A smartphone photograph of a skin lesion. The patient is Fitzpatrick phototype III. A male patient in their 30s.
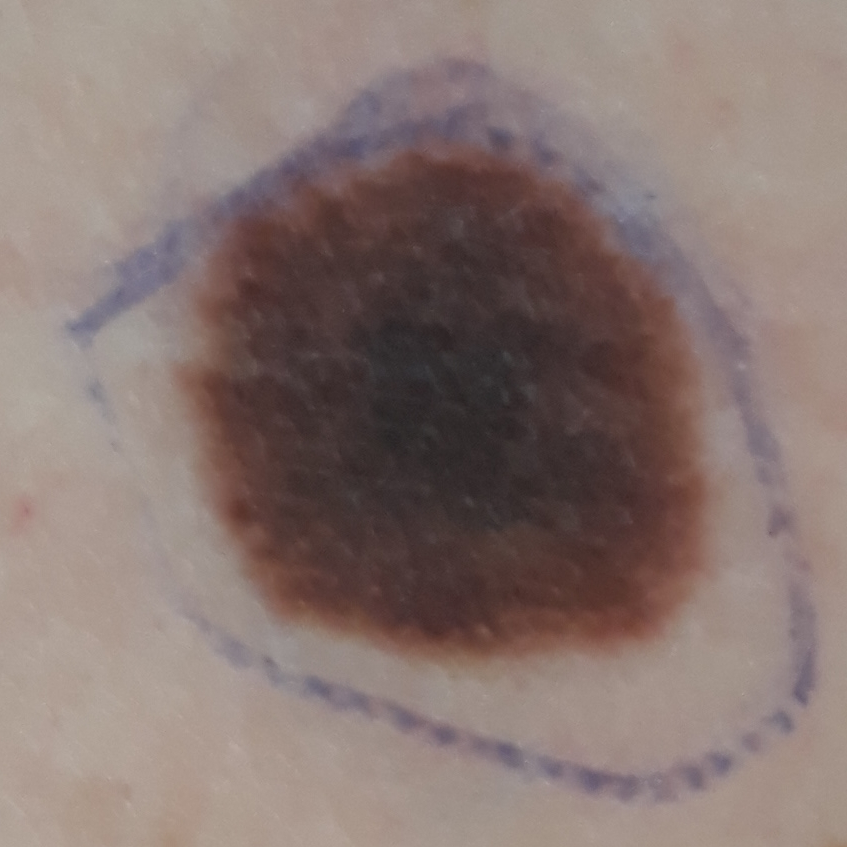Summary: Located on the back. The lesion is roughly 15 by 12 mm. Per patient report, the lesion does not itch. Diagnosis: Histopathologically confirmed as a benign skin lesion — a nevus.